A dermoscopic image of a skin lesion · on a questionnaire the patient reported a prior organ transplant · few moles overall by the patient's own estimate · collected as part of a research study, without a referral diagnosis · the patient says their skin reddens with sun exposure · a male patient 66 years old — 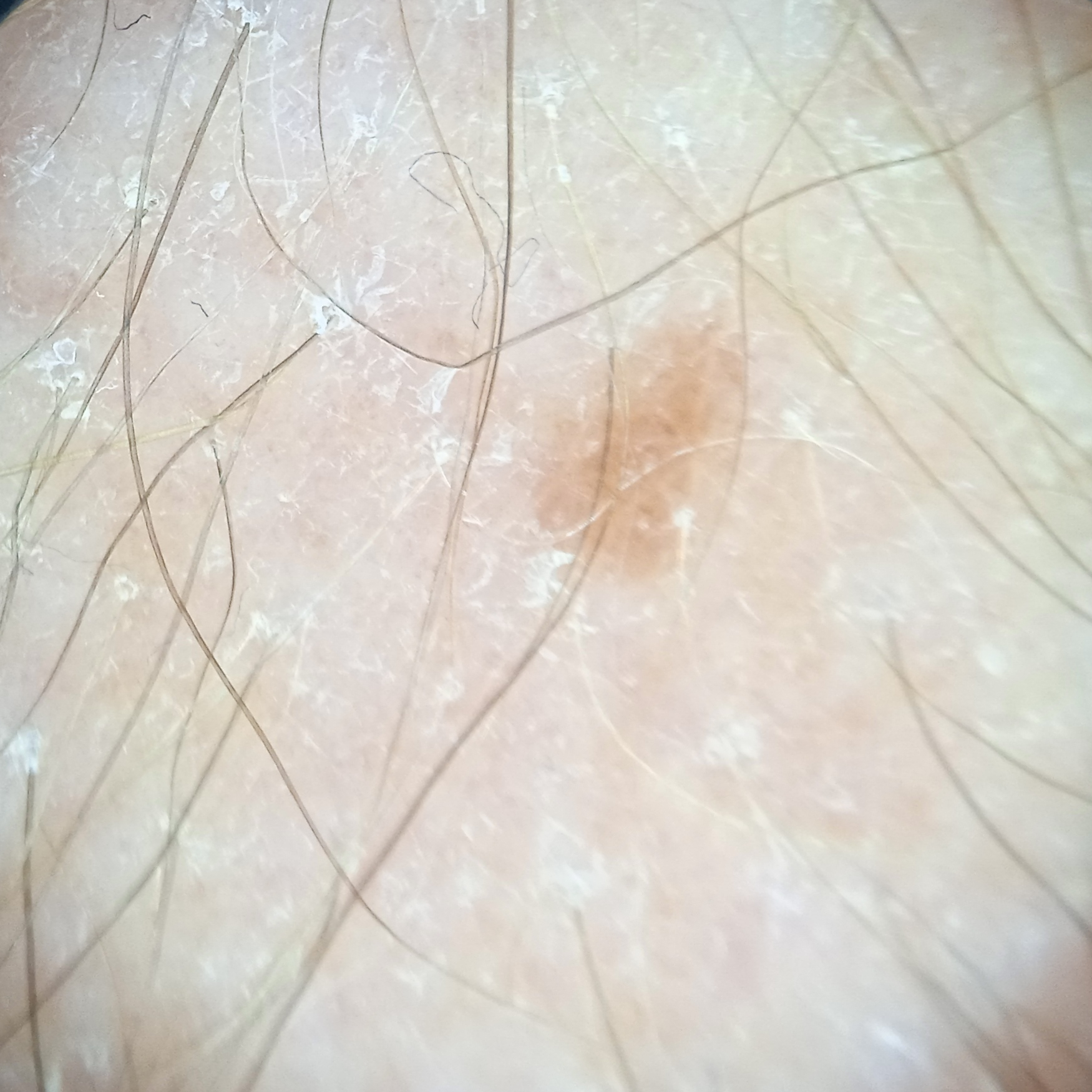| field | value |
|---|---|
| body site | an arm |
| lesion size | 3.4 mm |
| assessment | melanocytic nevus (dermatologist consensus) |